The subject is a female aged 40–49; an image taken at an angle.
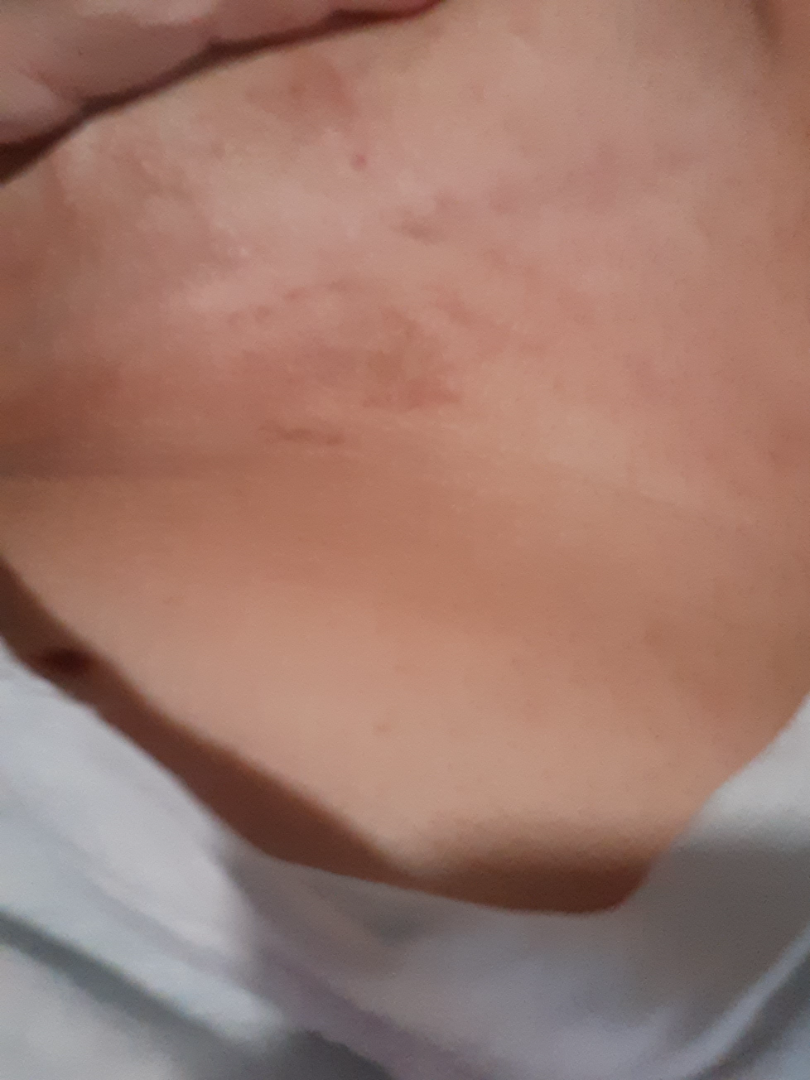<dermatology_case>
  <skin_tone>
    <fitzpatrick>III</fitzpatrick>
  </skin_tone>
  <patient_category>a rash</patient_category>
  <duration>less than one week</duration>
  <differential>Eczema</differential>
</dermatology_case>